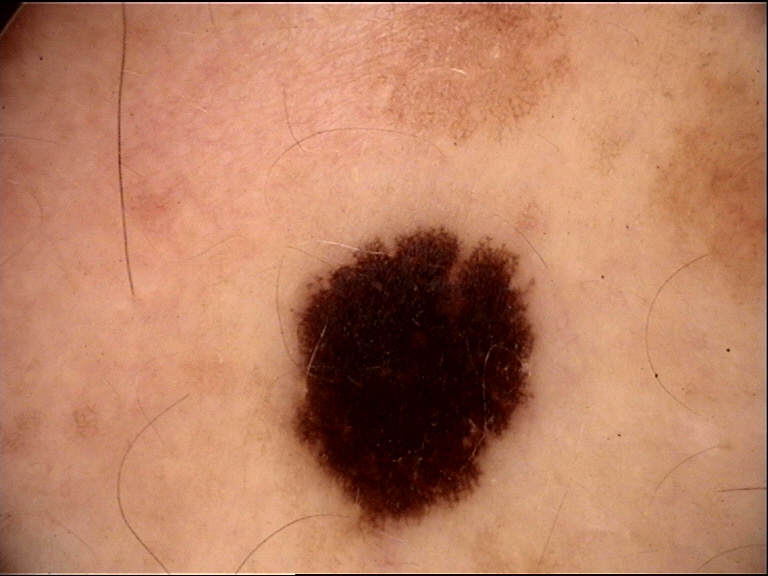Findings: A dermoscopic close-up of a skin lesion. Impression: The diagnostic label was a benign lesion — a dysplastic junctional nevus.